A female subject 90 years old · history notes prior malignancy (patient or family) · recorded as skin type I · a smartphone photograph of a skin lesion.
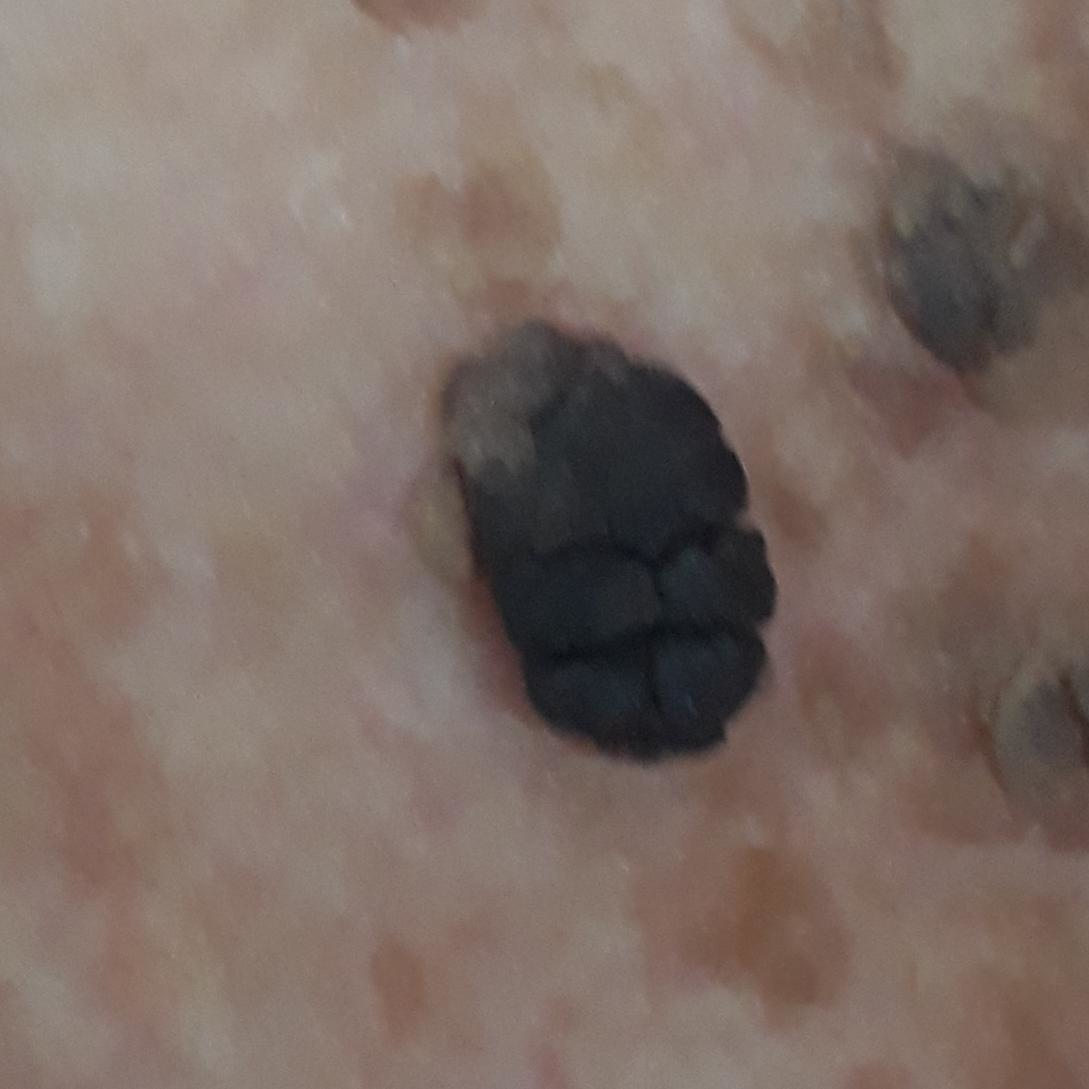  lesion_location: the neck
  lesion_size:
    diameter_1_mm: 13.0
    diameter_2_mm: 7.0
  symptoms:
    present:
      - elevation
      - growth
      - itching
  diagnosis:
    name: seborrheic keratosis
    code: SEK
    malignancy: benign
    confirmation: clinical consensus